A dermoscopic view of a skin lesion · the patient is a male aged around 75:
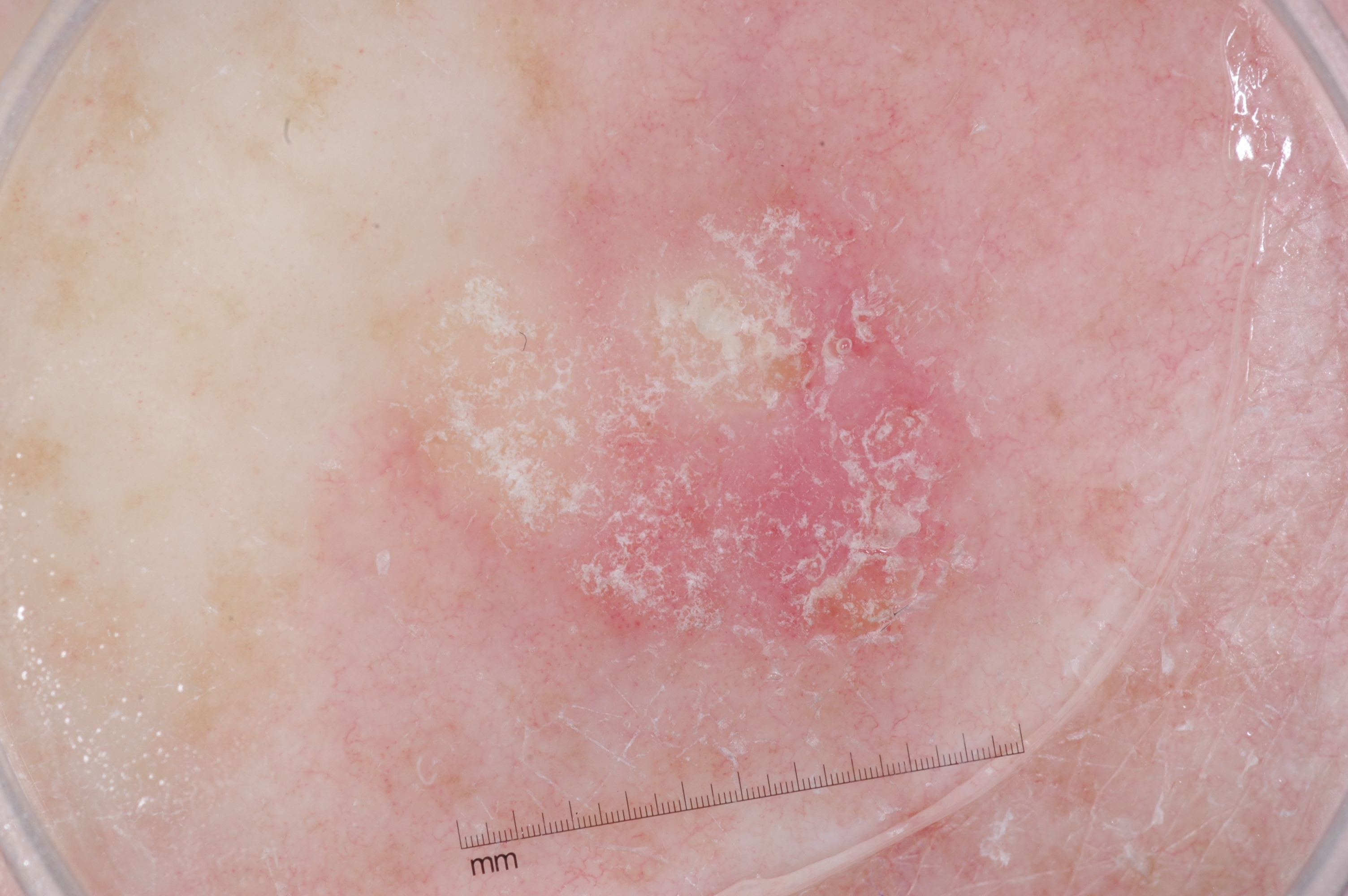Image and clinical context: Dermoscopic review identifies no milia-like cysts, negative network, streaks, or pigment network. The visible lesion spans [340, 39, 1047, 741]. The lesion occupies roughly 31% of the field. Conclusion: Consistent with a seborrheic keratosis, a keratinocytic lesion.